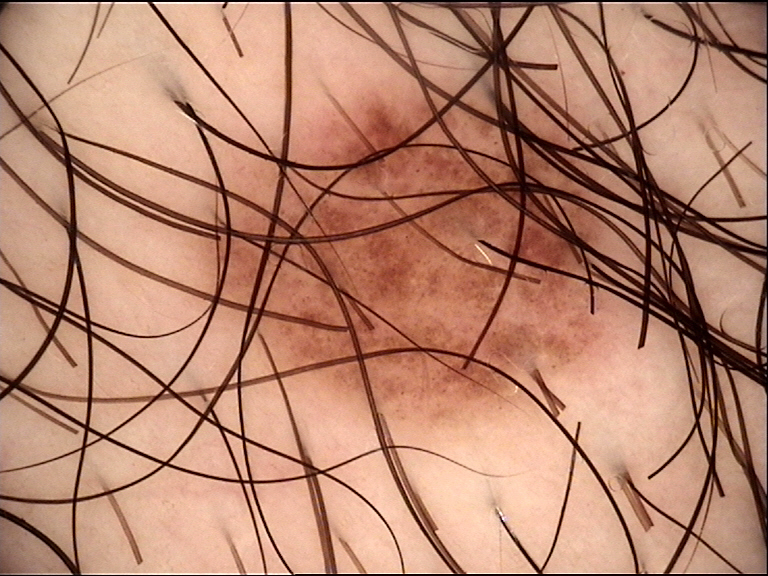Classified as a dysplastic compound nevus.